A dermoscopic view of a skin lesion · a male subject aged around 55:
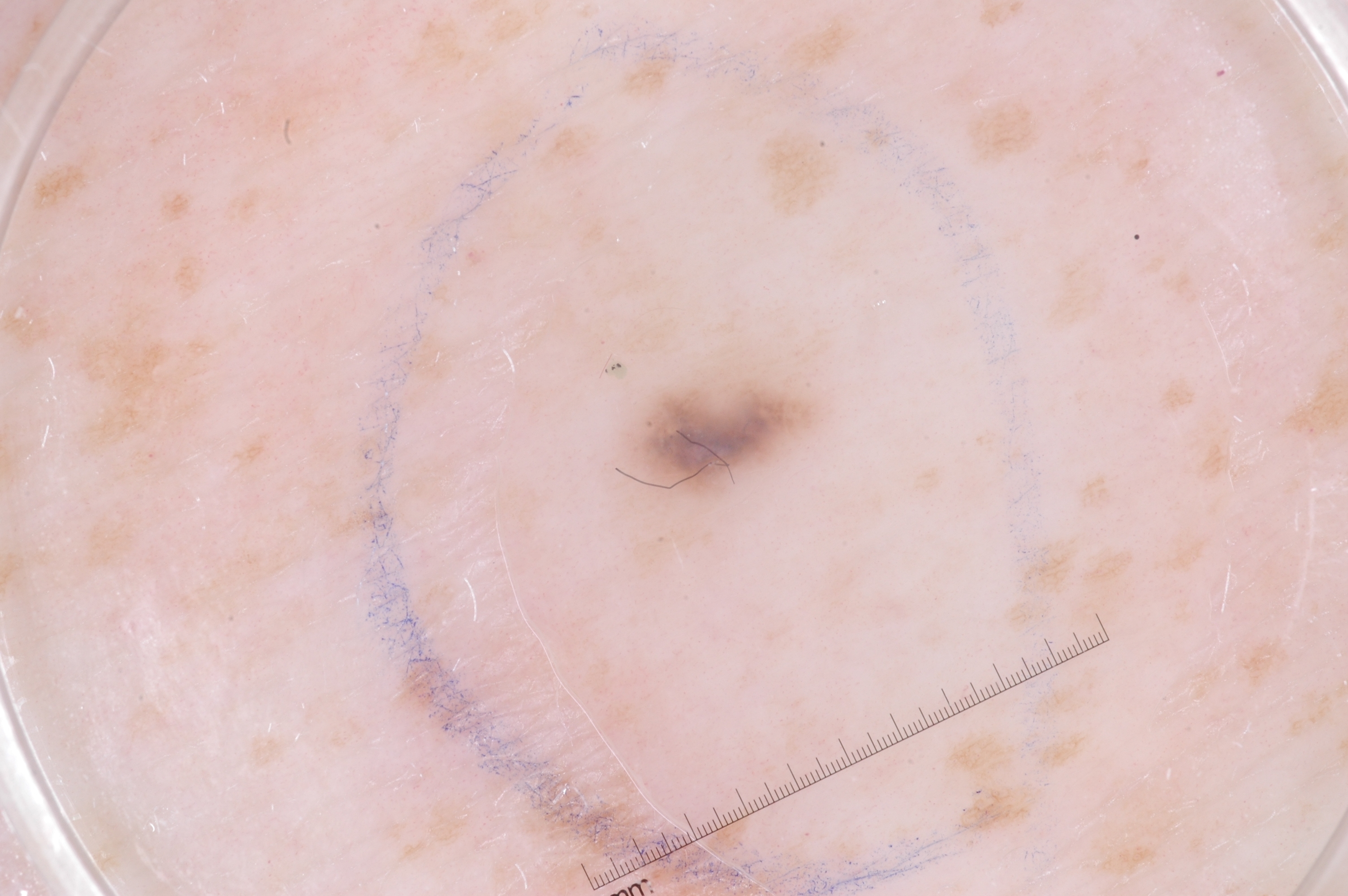{"dermoscopic_features": {"present": [], "absent": ["milia-like cysts", "streaks", "pigment network", "negative network"]}, "lesion_extent": {"approx_field_fraction_pct": 3}, "lesion_location": {"bbox_xyxy": [611, 315, 832, 532]}, "diagnosis": {"name": "melanocytic nevus", "malignancy": "benign", "lineage": "melanocytic", "provenance": "clinical"}}